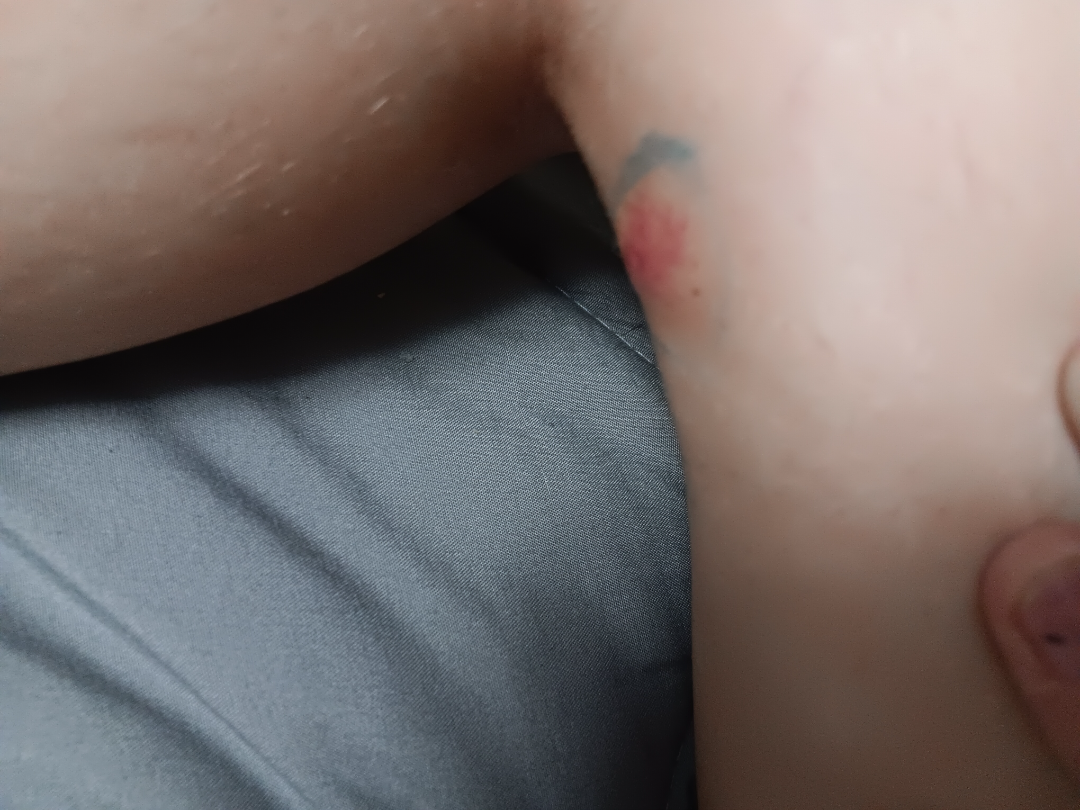The affected area is the leg.
The subject is a female aged 18–29.
This image was taken at an angle.
On photographic review: Abscess (considered); Insect Bite (considered); B-Cell Cutaneous Lymphoma (lower probability).